The sole of the foot is involved. The photograph is a close-up of the affected area. Female patient, age 50–59 — 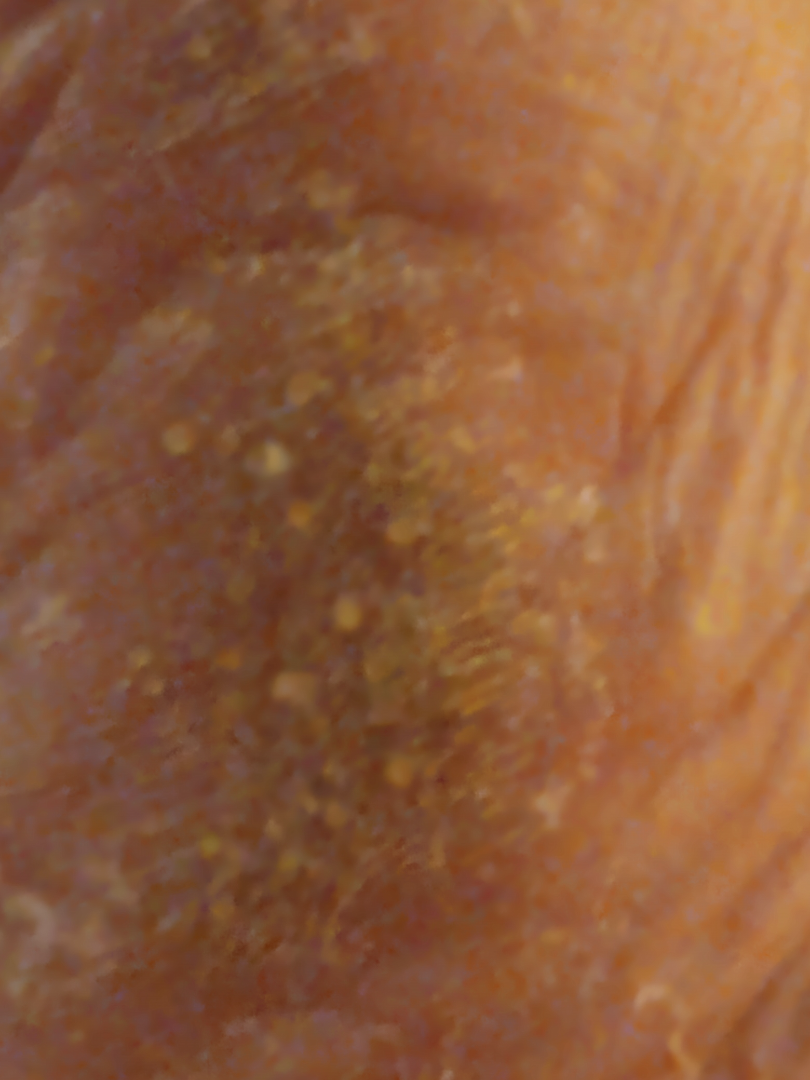Findings: The skin condition could not be confidently assessed from this image. Background: Reported lesion symptoms include pain. Self-reported FST VI. The contributor reports the condition has been present for one to three months. No constitutional symptoms were reported. Texture is reported as rough or flaky.